A dermoscopic view of a skin lesion; a female patient about 30 years old: 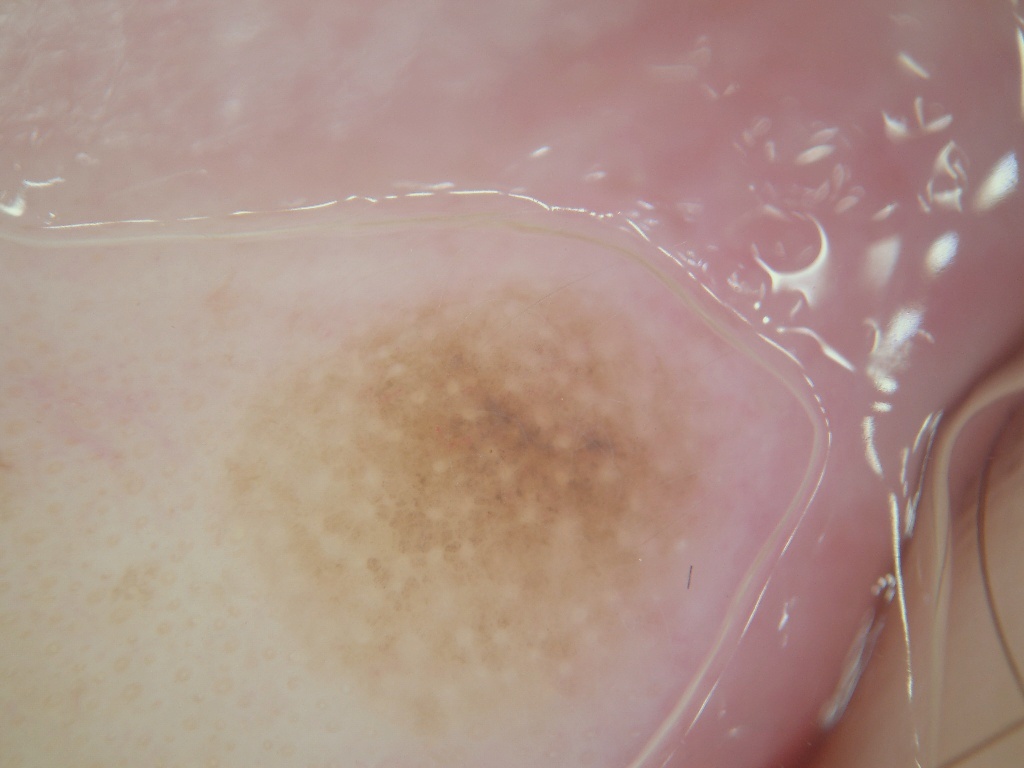- location — [192,270,752,741]
- extent — ~25% of the field
- dermoscopic features assessed but absent — milia-like cysts, streaks, globules, negative network, and pigment network
- diagnostic label — a melanocytic nevus, a benign lesion